A skin lesion imaged with a dermatoscope.
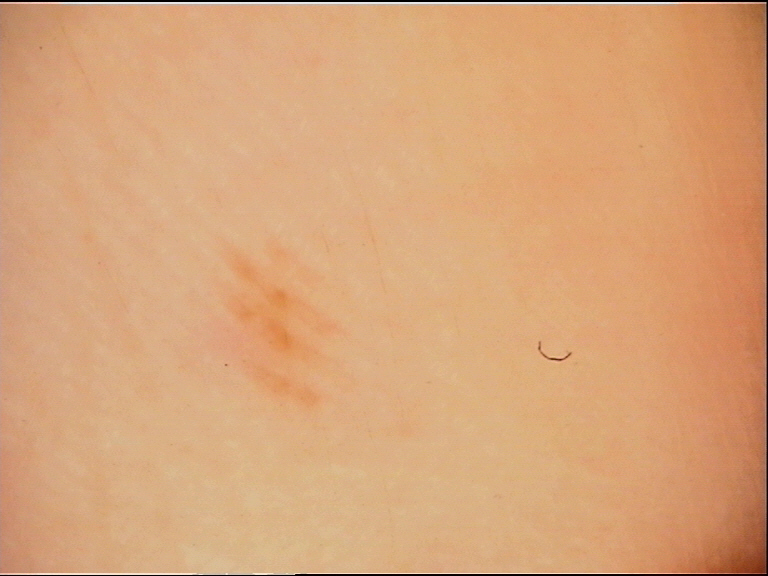Case:
This is a banal lesion.
Impression:
Diagnosed as an acral junctional nevus.